Reported duration is one to four weeks, the patient considered this a rash, the contributor notes itching and enlargement, the photograph is a close-up of the affected area, the affected area is the leg and front of the torso, texture is reported as raised or bumpy: 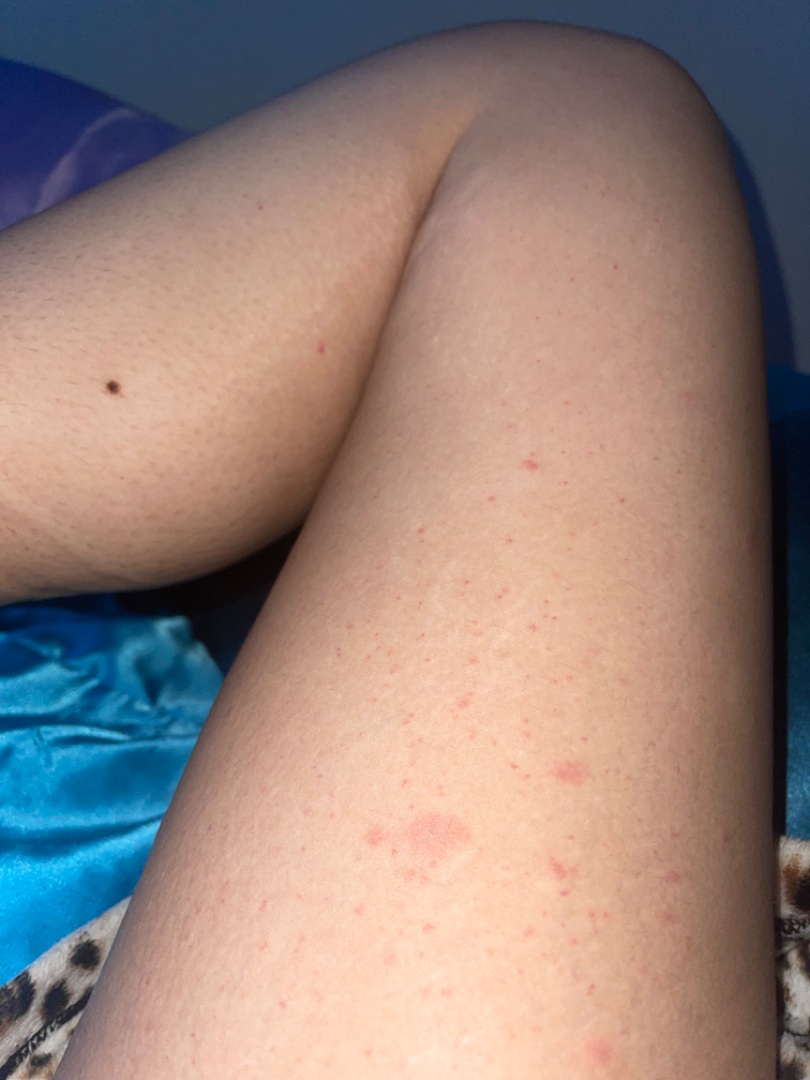Review:
The reviewing panel's impression was: the leading consideration is Viral Exanthem; lower on the differential is Pityriasis rosea; less likely is Allergic Contact Dermatitis; less probable is Drug Rash; a more distant consideration is Hypersensitivity.